The photo was captured at a distance; located on the leg; reported duration is one to four weeks; the patient considered this a rash.
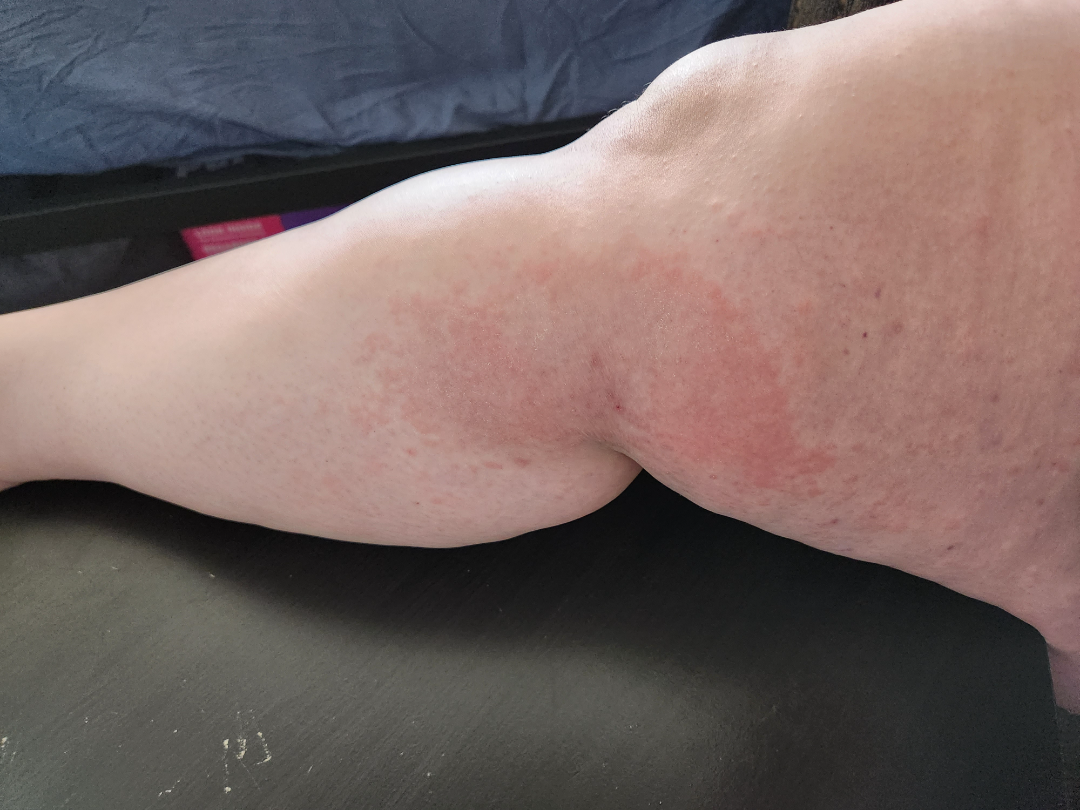Assessment:
Three dermatologists each reviewed the case: most likely Eczema; a remote consideration is Urticaria; lower on the differential is Allergic Contact Dermatitis.